Present for less than one week; an image taken at a distance; texture is reported as flat and raised or bumpy; the lesion is associated with bothersome appearance; the contributor is a male aged 40–49; located on the back of the torso; self-categorized by the patient as a rash — 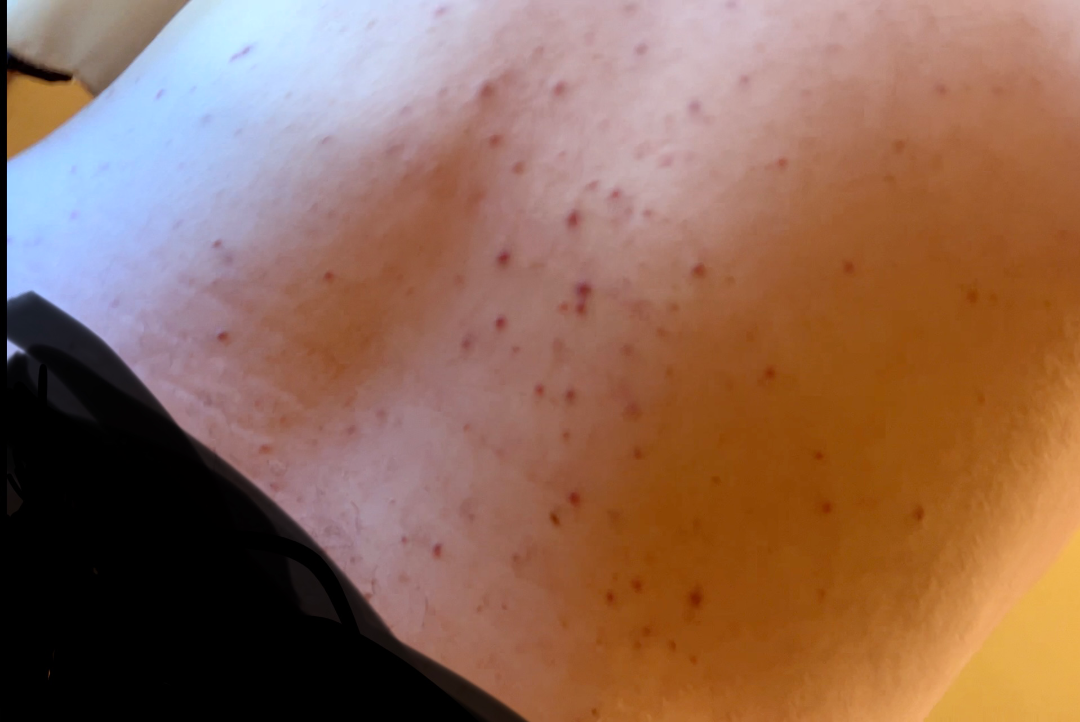{"differential": {"leading": ["Leukocytoclastic Vasculitis"], "considered": ["Pityriasis lichenoides", "Folliculitis"]}}